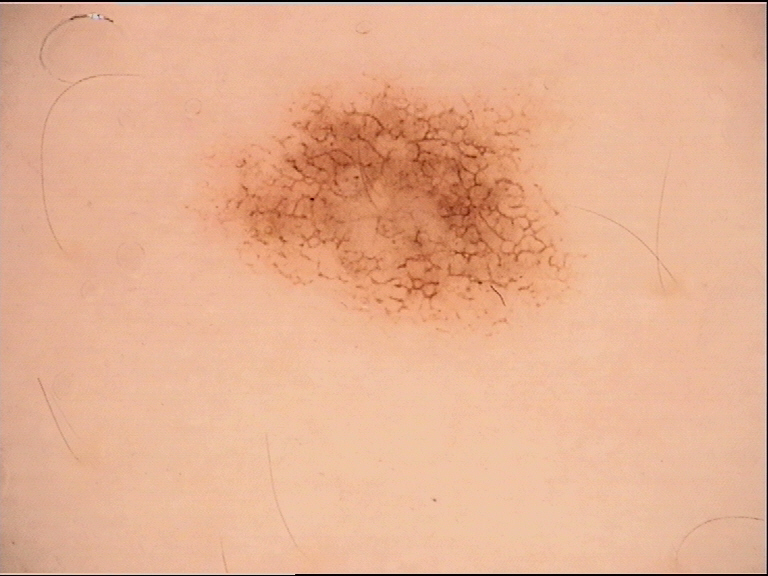diagnosis: dysplastic junctional nevus (expert consensus).